The chart records alcohol use, prior malignancy (patient or family), and prior skin cancer (patient or family); a male patient aged 71; a clinical photograph of a skin lesion; the patient was assessed as FST II: 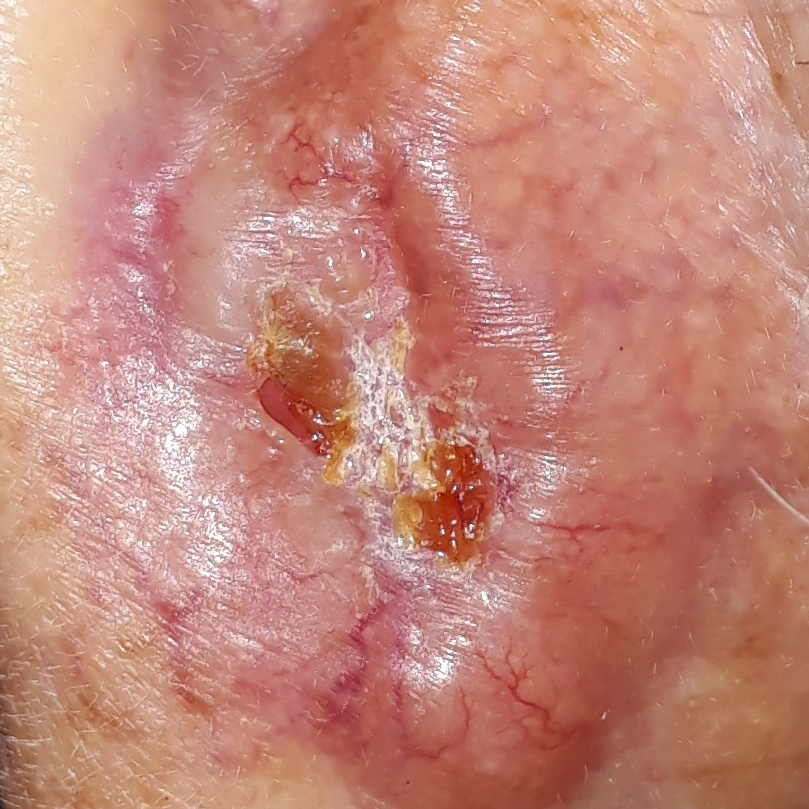Q: What is the anatomic site?
A: an ear
Q: What are the lesion's dimensions?
A: 25x18 mm
Q: What symptoms does the patient report?
A: bleeding, itching, pain, elevation
Q: What is this lesion?
A: basal cell carcinoma (biopsy-proven)